The affected area is the arm. The condition has been present for one to four weeks. Associated systemic symptoms include mouth sores and shortness of breath. The subject is female. The patient reports the lesion is flat. This image was taken at an angle — 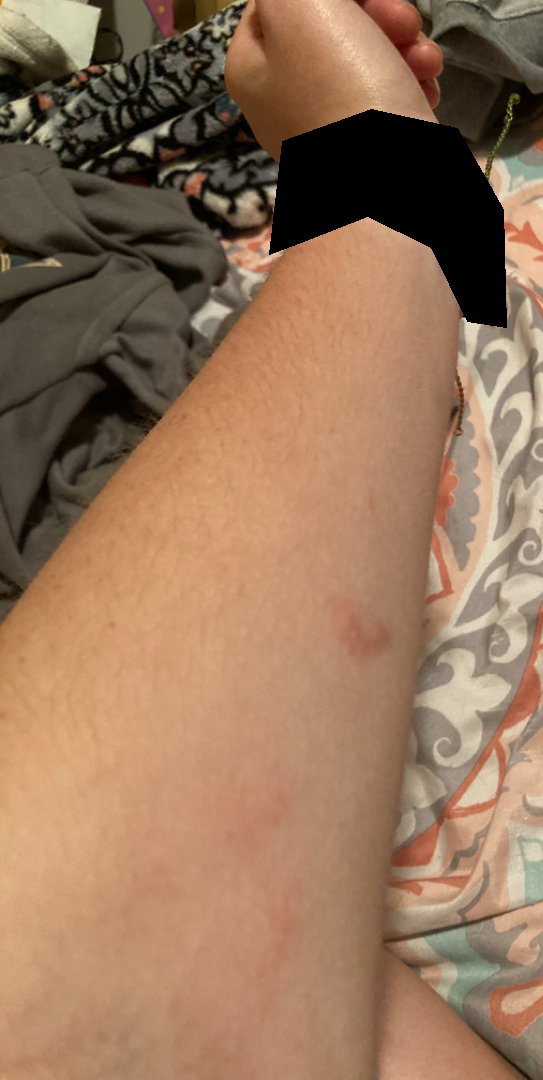differential diagnosis — Contact dermatitis (leading); Pigmented purpuric eruption (considered); Morphea/Scleroderma (considered); Post-Inflammatory hyperpigmentation (considered).